A female subject, aged 43-47. A dermoscopic close-up of a skin lesion.
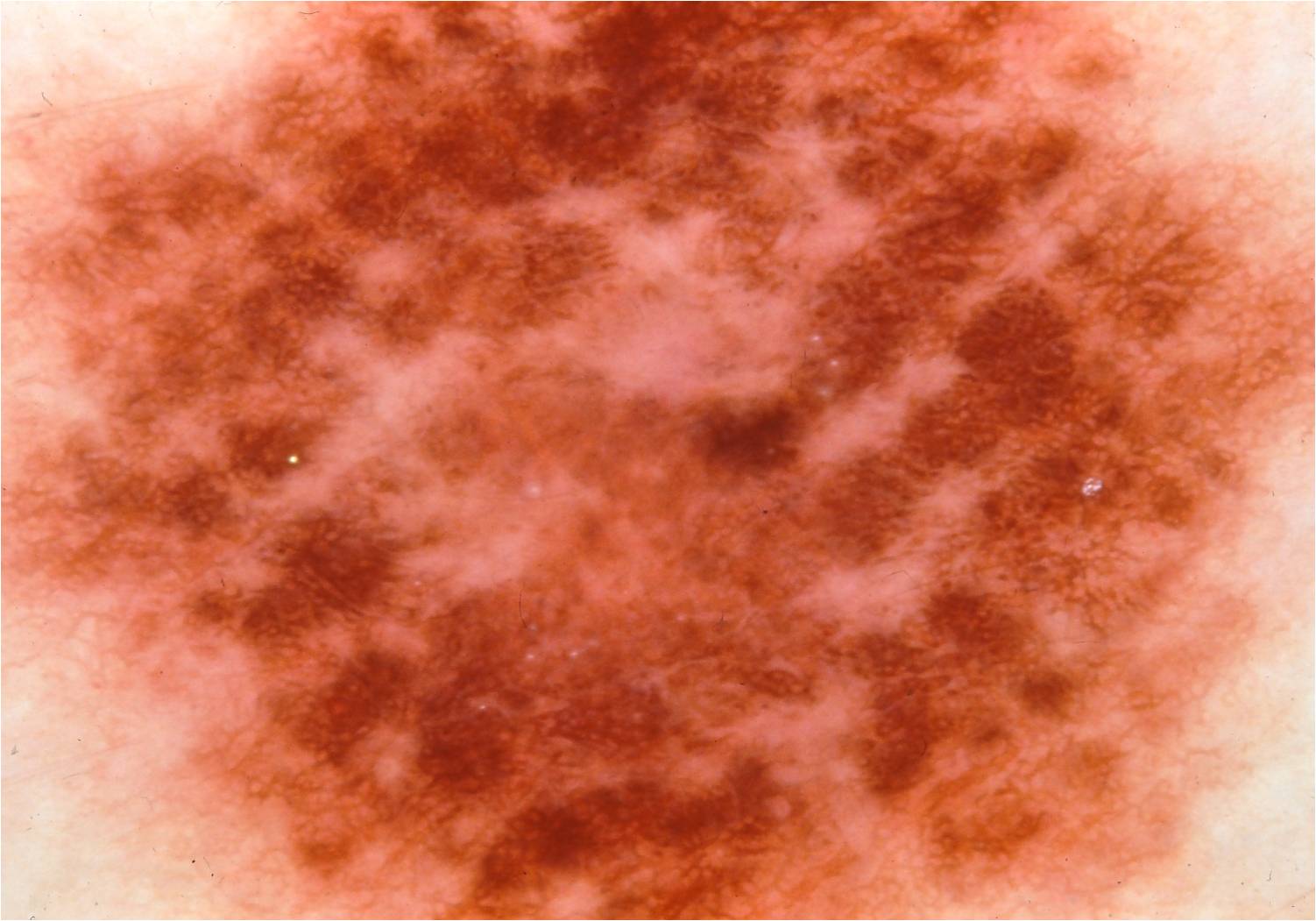features = globules, pigment network, and negative network | location = spans the dermoscopic field | impression = a melanocytic nevus, a benign skin lesion.